A skin lesion imaged with a dermatoscope:
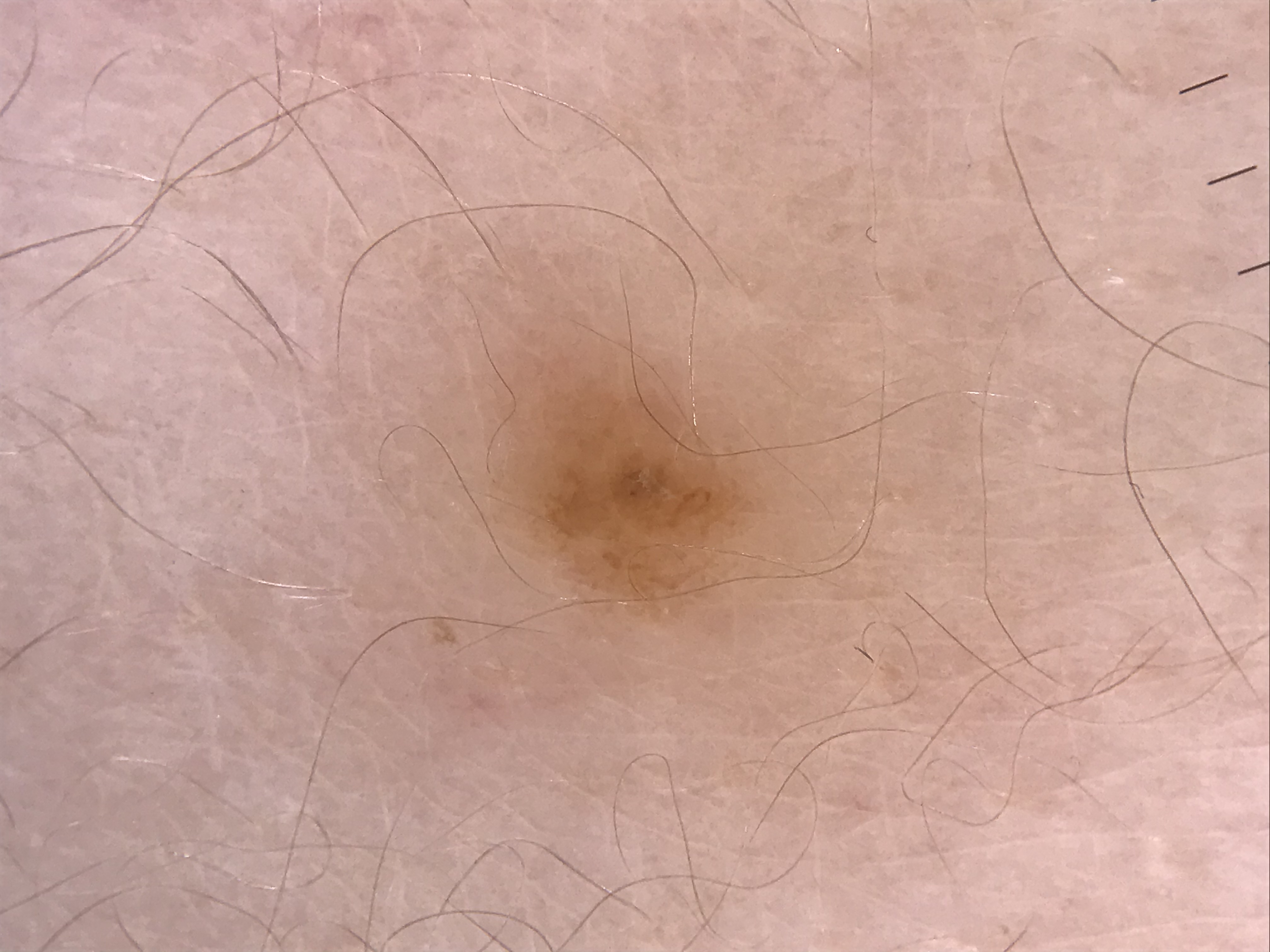diagnosis: junctional nevus (expert consensus).